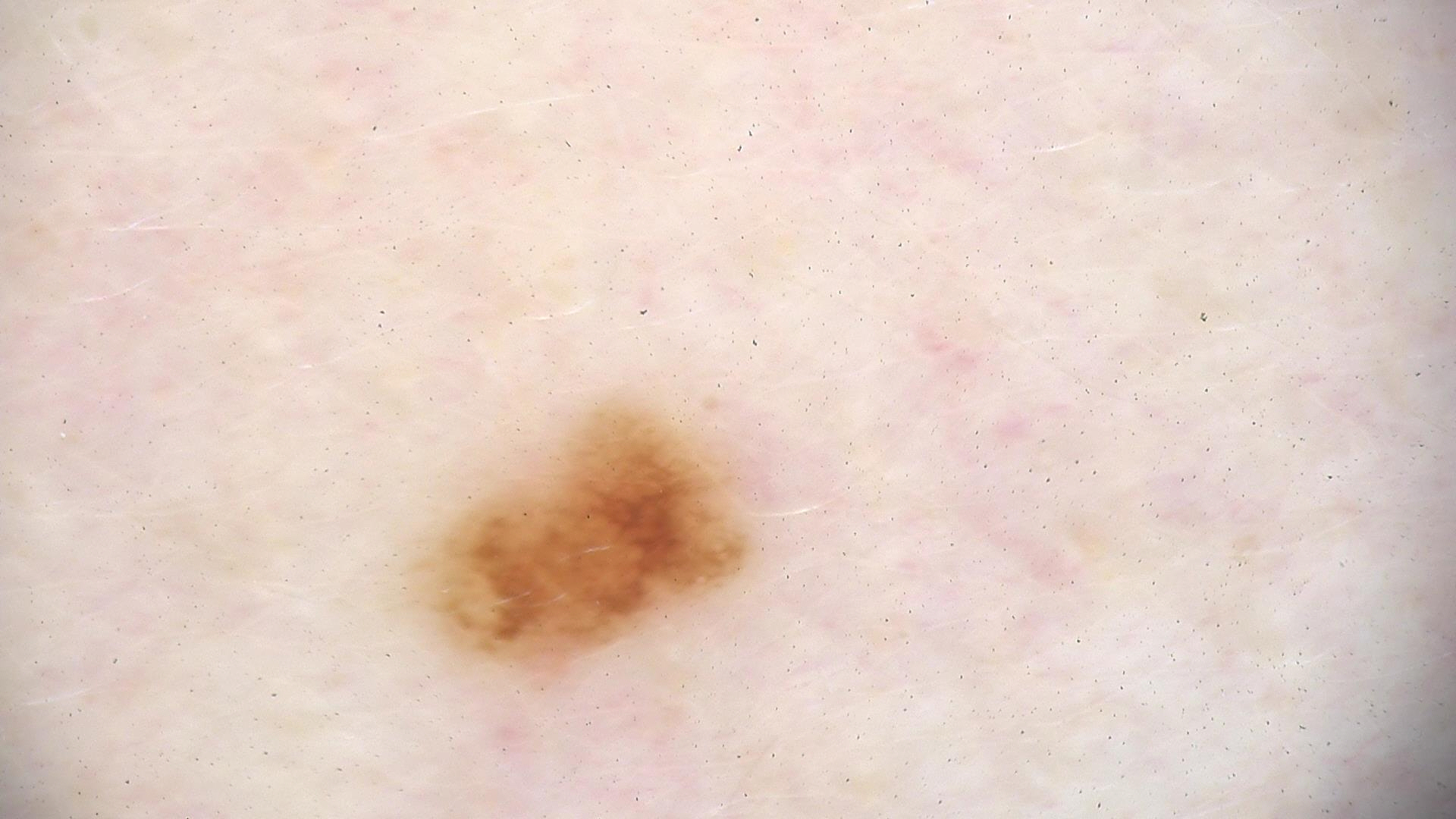Case: Dermoscopy of a skin lesion. Impression: Classified as a benign lesion — a dysplastic junctional nevus.